The photo was captured at a distance · female contributor, age 50–59 · reported lesion symptoms include bothersome appearance · the patient notes the lesion is flat · located on the sole of the foot, front of the torso and leg · the patient notes the condition has been present for more than five years · self-categorized by the patient as a pigmentary problem: 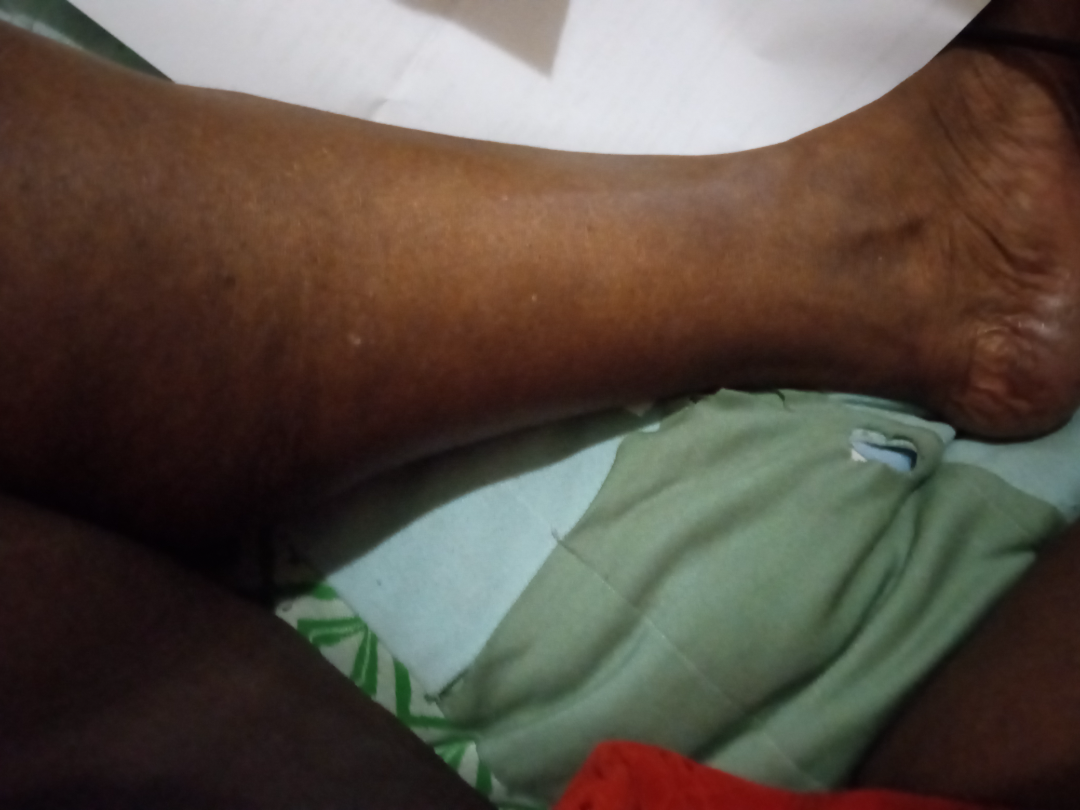  assessment: no clear pathology